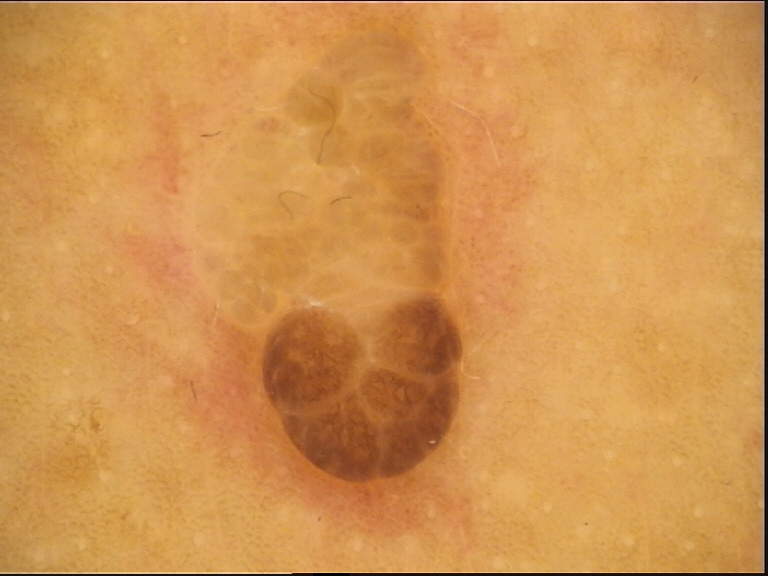image = dermoscopy | subtype = banal | diagnostic label = dermal nevus (expert consensus).